This is a close-up image: 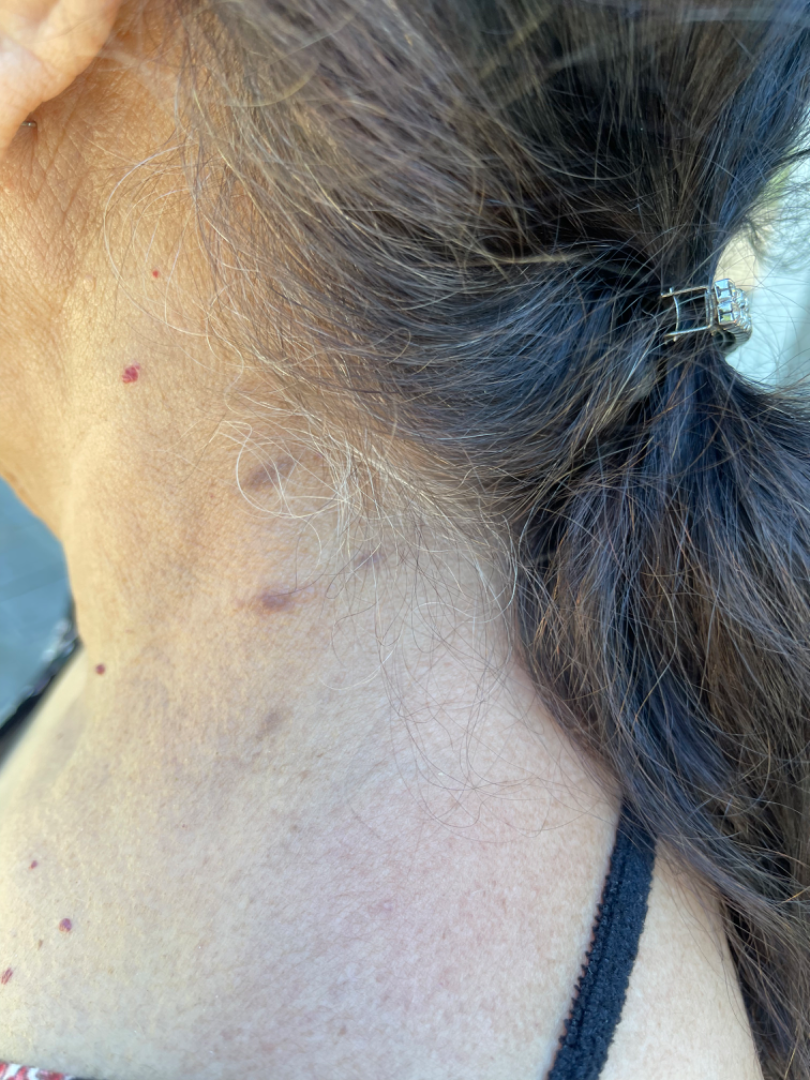Review:
On dermatologist assessment of the image, Actinic Keratosis (0.33); Lichen planus/lichenoid eruption (0.33); Post-Inflammatory hyperpigmentation (0.33).